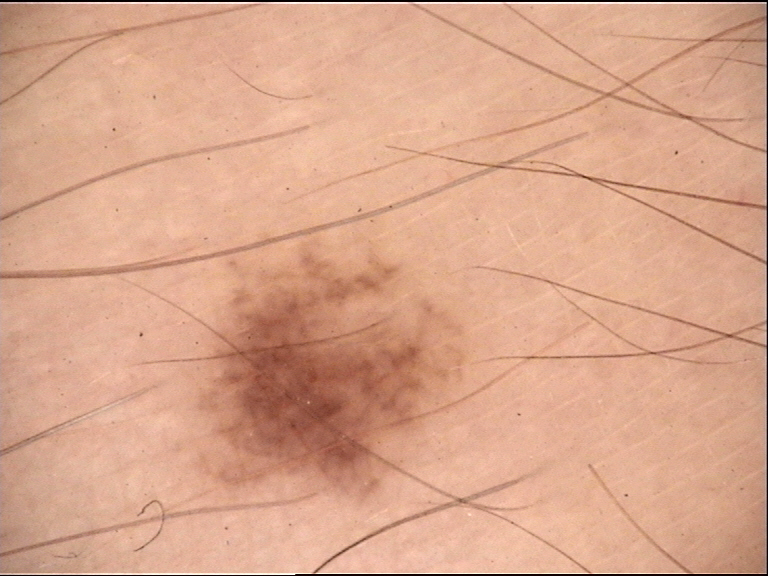A dermoscopic close-up of a skin lesion. Labeled as a banal lesion — a junctional nevus.